The subject is a male aged 18–29; the patient described the issue as a rash; the condition has been present for one to four weeks; the patient reported no systemic symptoms; the contributor reports the lesion is rough or flaky; the photo was captured at an angle; the lesion is associated with darkening; the lesion involves the back of the hand.
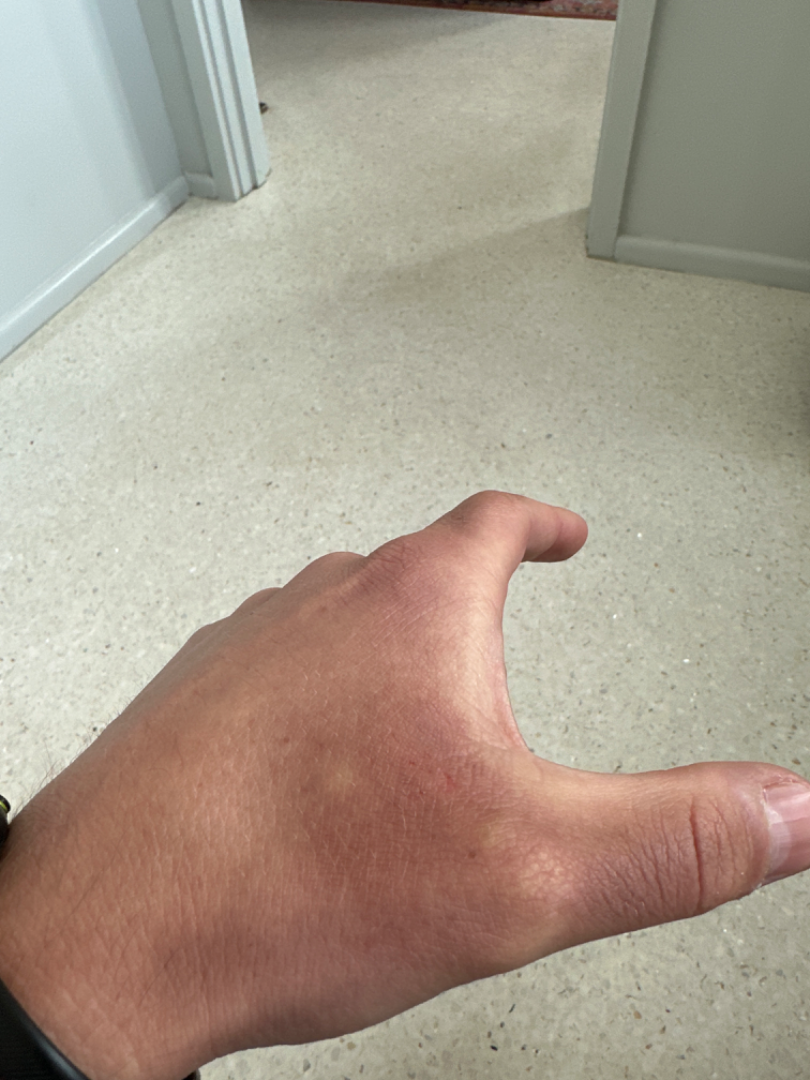| key | value |
|---|---|
| assessment | not assessable |